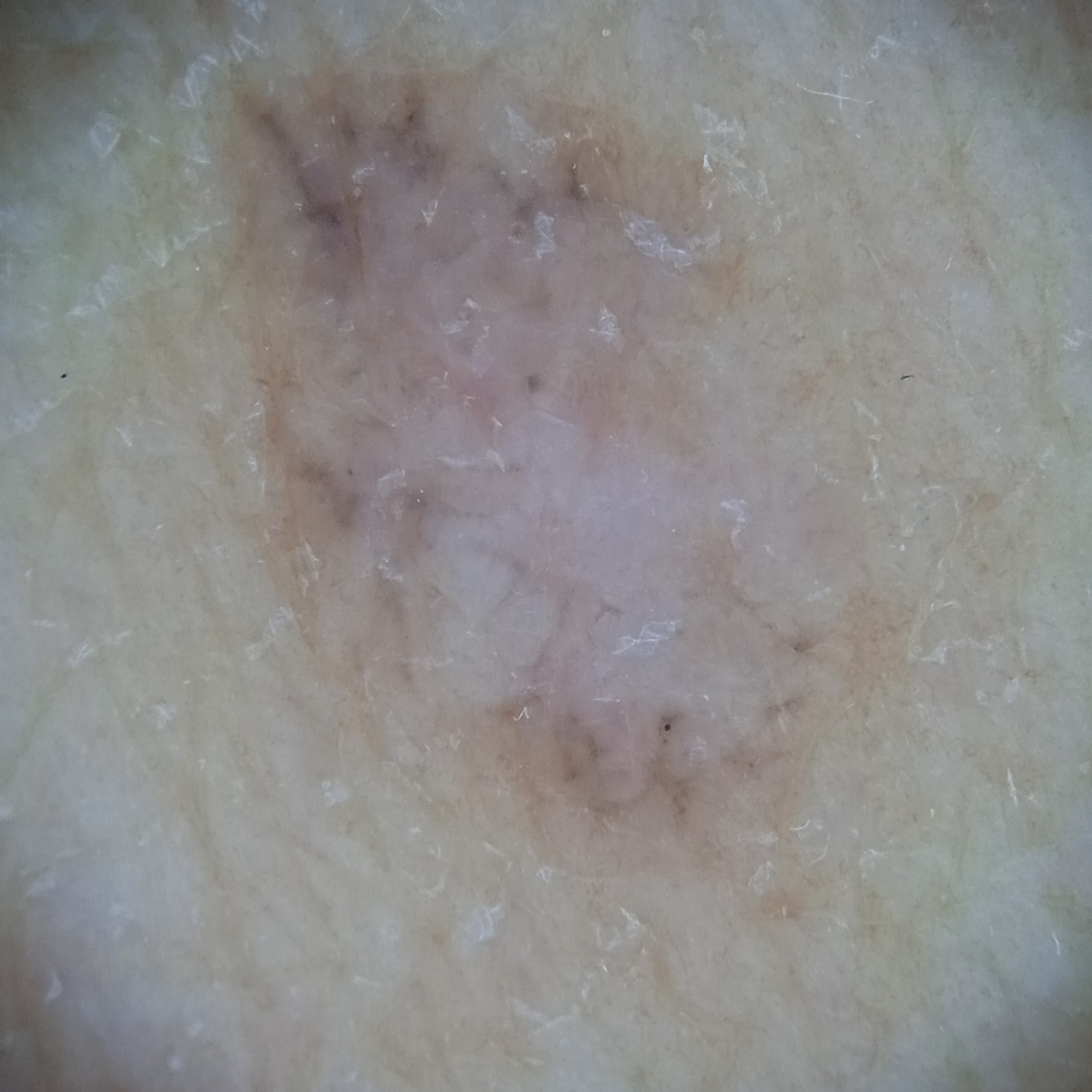Case summary:
A female patient 60 years of age. By self-report, a personal history of skin cancer and a personal history of cancer. The patient says their skin tans without first burning. The patient describes having few moles overall. Imaged for a research study, with no referral diagnosis recorded. A skin lesion imaged with a dermatoscope. The lesion is located on the back. The lesion is about 10.4 mm across.
Impression:
The dermatologists' assessment was a basal cell carcinoma.